A female patient in their mid-20s · this is a dermoscopic photograph of a skin lesion — 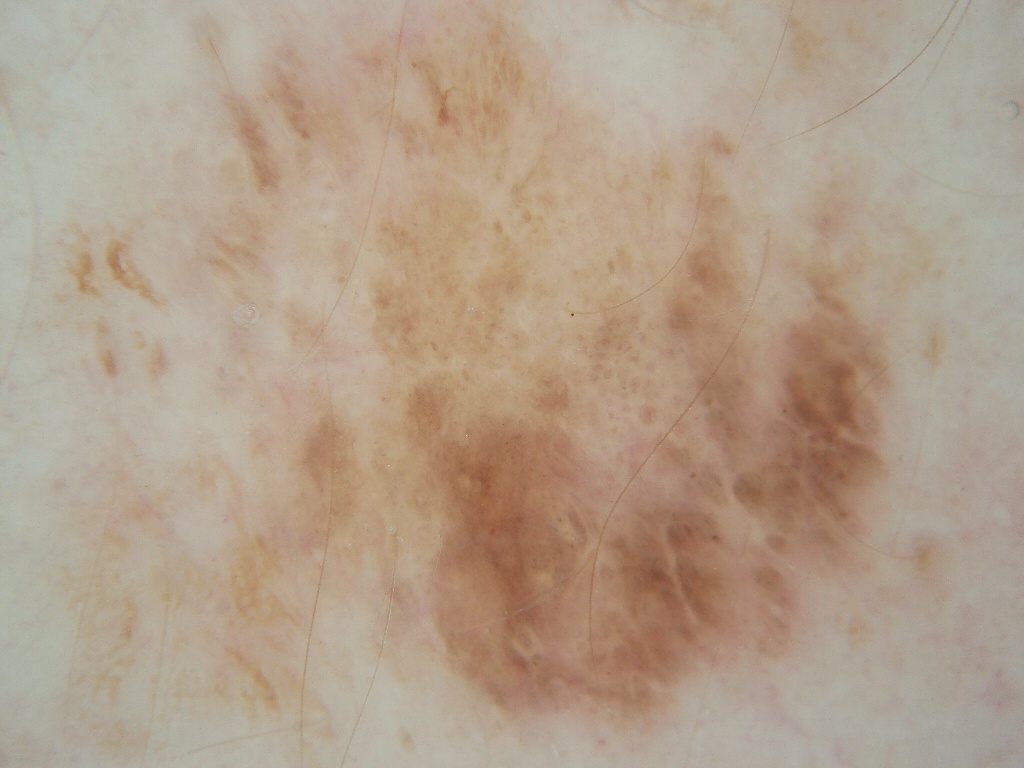Notes:
– dermoscopic pattern: negative network, pigment network, and globules
– location: reaches across the whole image
– diagnosis: a melanocytic nevus, a benign skin lesion